The subject is a female aged 60–69; an image taken at a distance; the patient reported no systemic symptoms; the lesion is associated with itching; located on the leg; self-categorized by the patient as a rash — 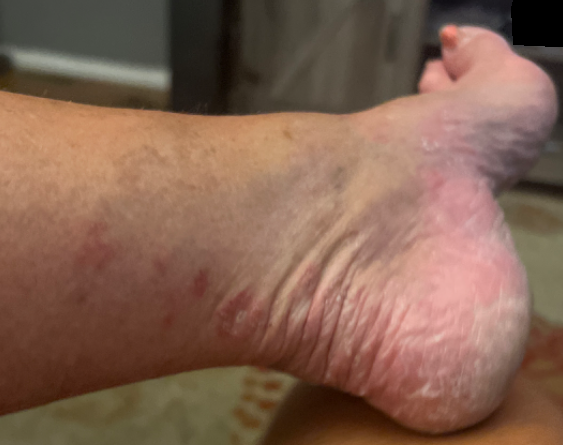The skin condition could not be confidently assessed from this image.